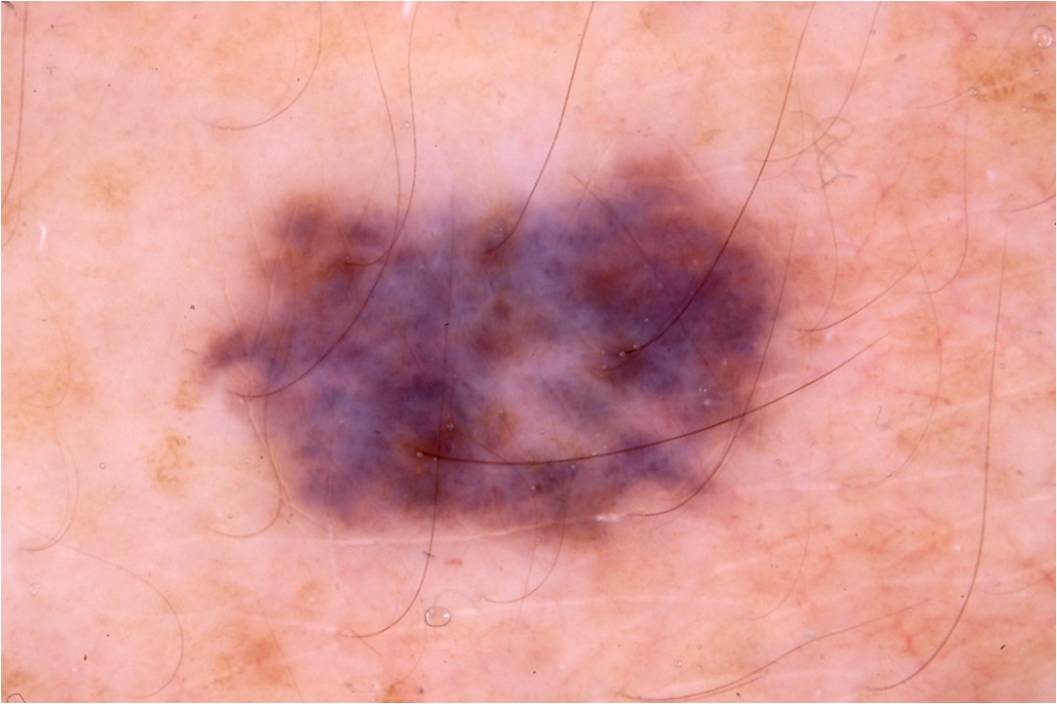Dermoscopy of a skin lesion. Dermoscopic examination shows no pigment network, milia-like cysts, negative network, globules, or streaks. In (x1, y1, x2, y2) order, the lesion occupies the region 145, 141, 825, 567. The lesion takes up about 31% of the image. The diagnostic assessment was a melanocytic nevus, a benign lesion.